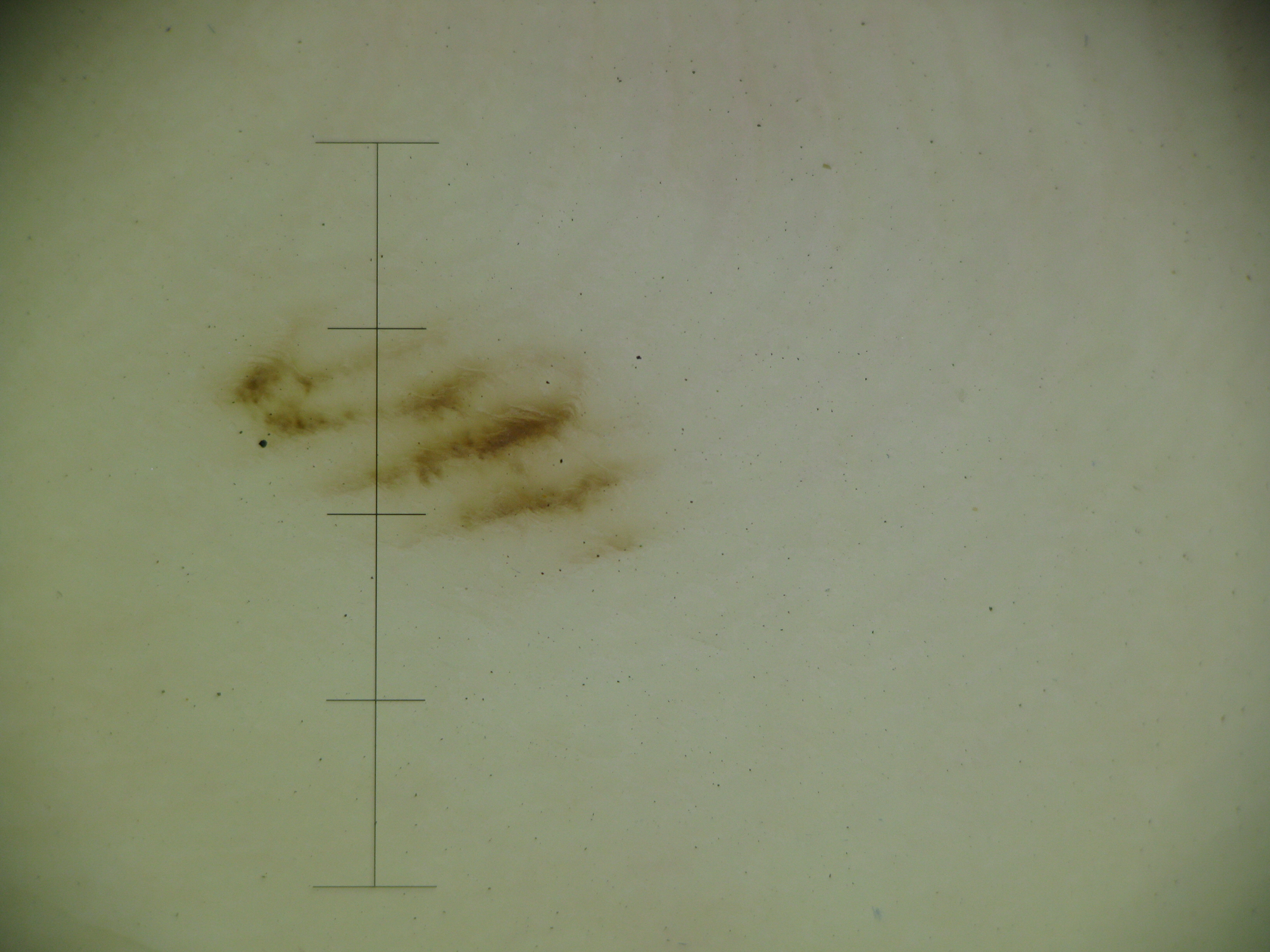imaging = dermatoscopy, subtype = banal, diagnostic label = acral junctional nevus (expert consensus).